A skin lesion imaged with a dermatoscope.
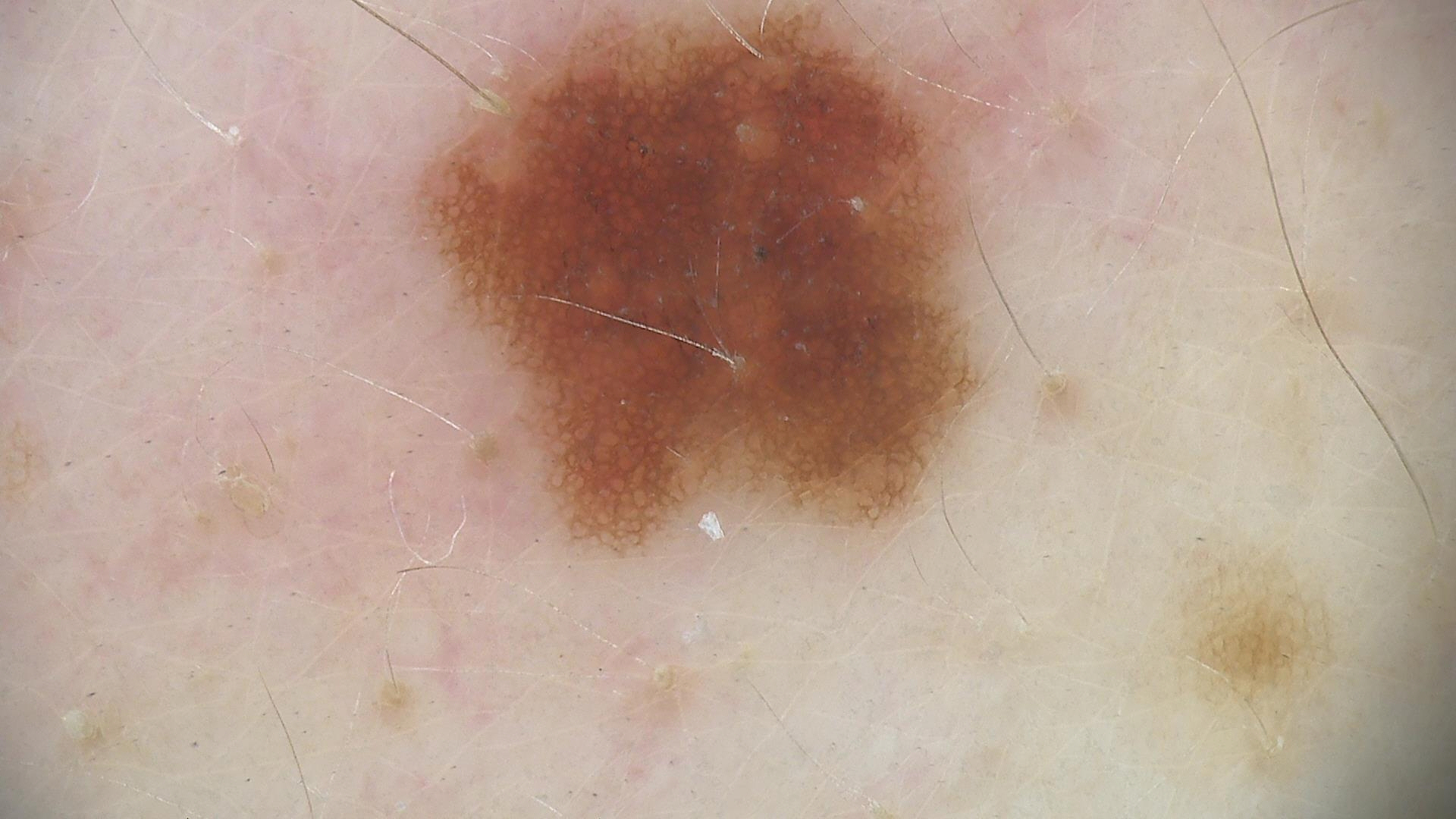diagnostic label=dysplastic junctional nevus (expert consensus).